An overview clinical photograph of a skin lesion · skin type II · a female subject approximately 80 years of age:
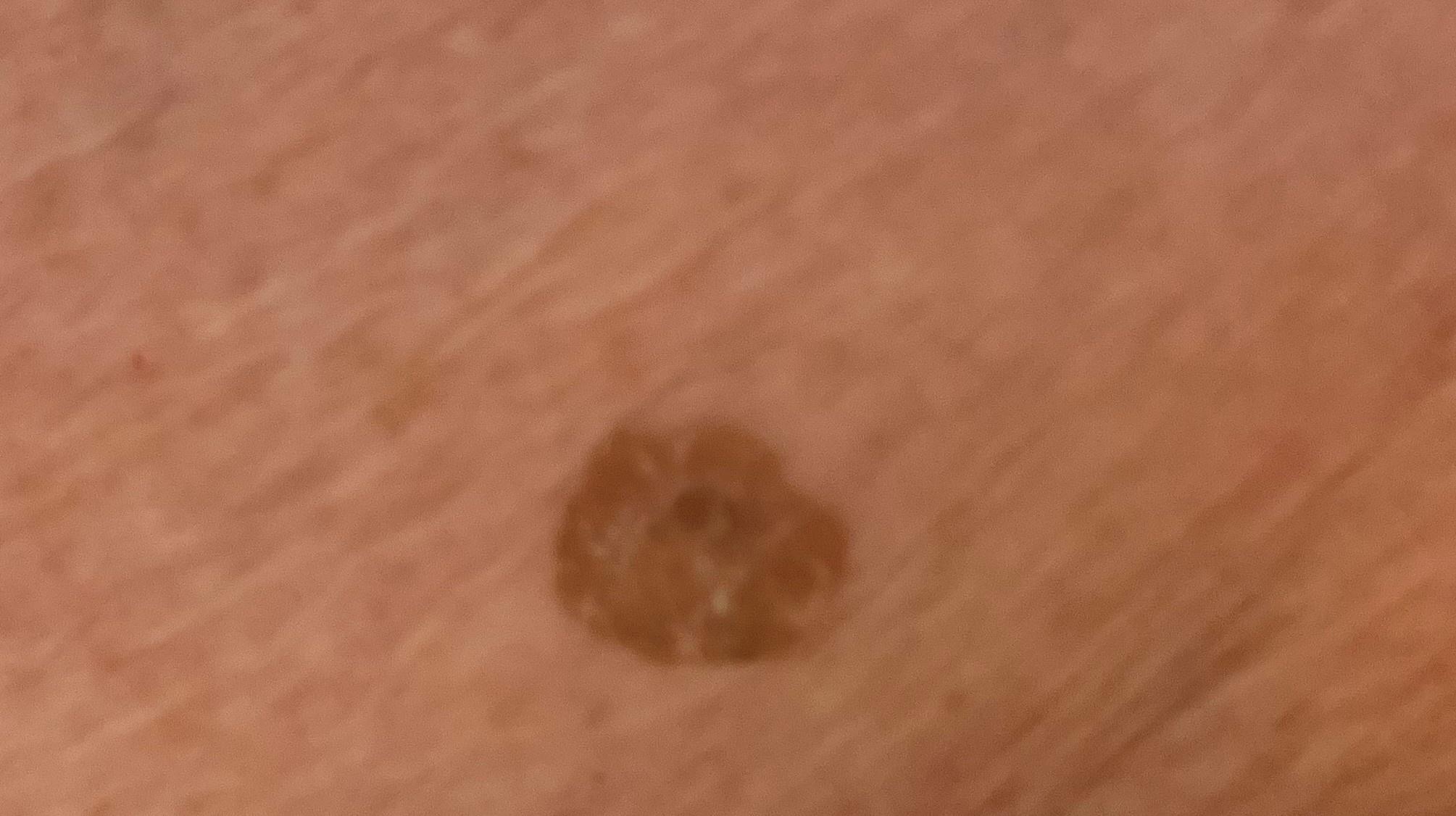The lesion was found on a lower extremity. Clinically diagnosed as a seborrheic keratosis.